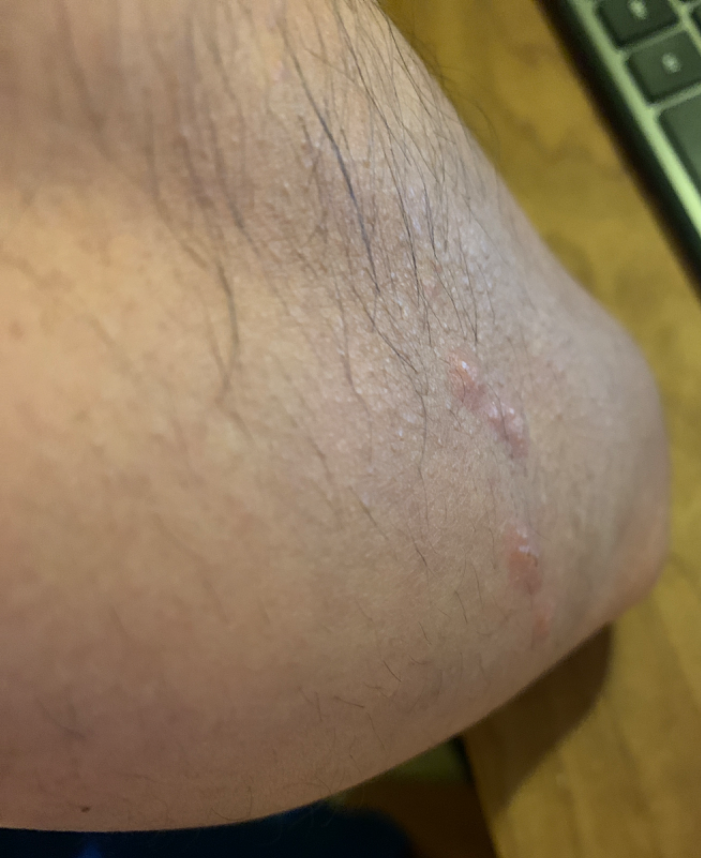Findings: The skin findings could not be characterized from the image. Background: No constitutional symptoms were reported. The patient considered this a rash. The contributor reports itching and bothersome appearance. The lesion is described as raised or bumpy. The lesion involves the arm. The photo was captured at an angle. Present for less than one week.